The photograph is a close-up of the affected area · the contributor notes the lesion is fluid-filled and raised or bumpy · located on the leg and arm — 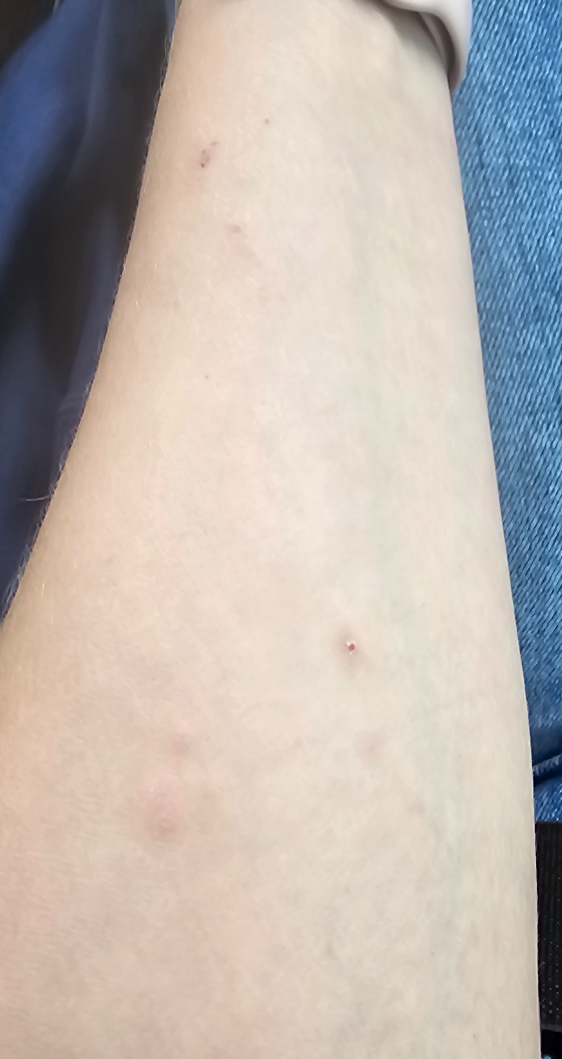Q: What was the assessment?
A: ungradable on photographic review